On a questionnaire the patient reported no personal history of cancer and no prior organ transplant · a dermoscopic image of a skin lesion · the patient says their skin tans without first burning · imaged for a research study, with no referral diagnosis recorded · the patient describes having numerous moles:
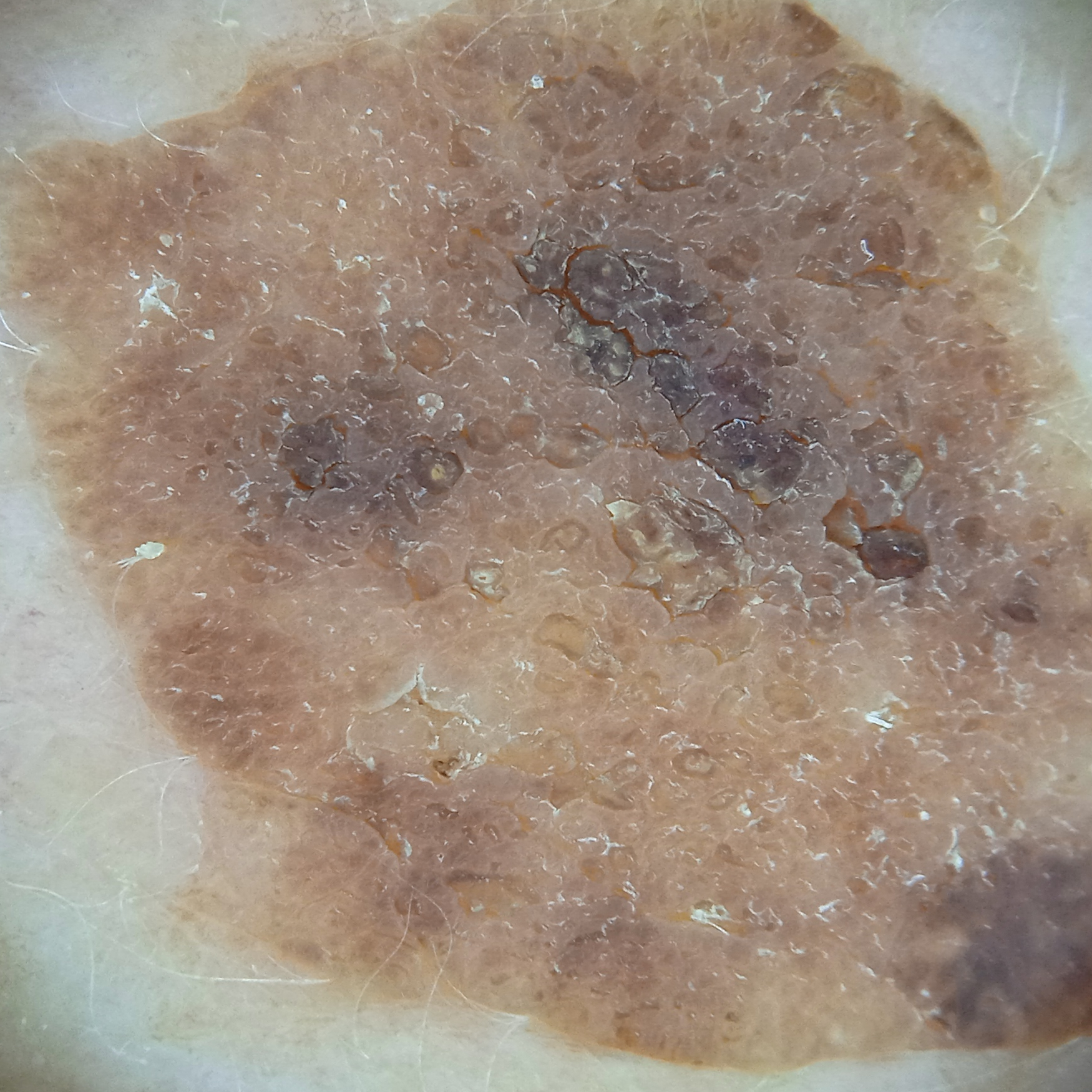The lesion is on the back.
The diagnostic impression was a seborrheic keratosis.